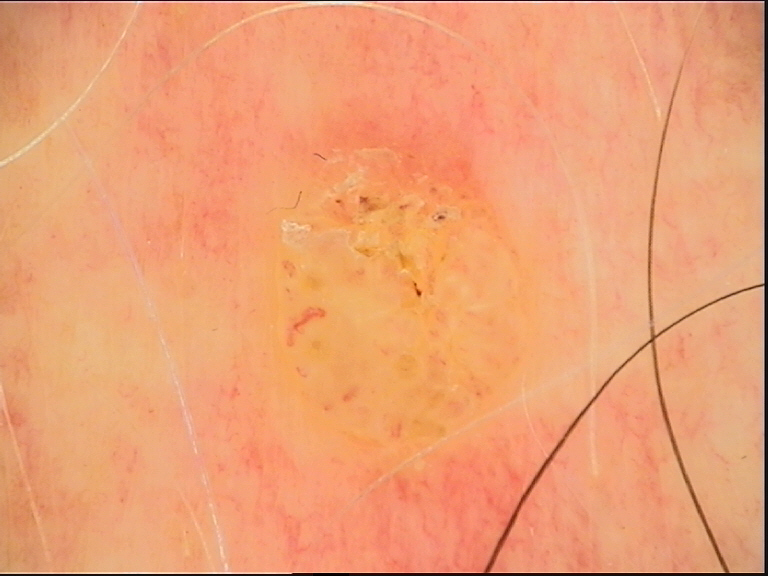Summary:
A dermoscopic close-up of a skin lesion.
Conclusion:
The diagnostic label was a seborrheic keratosis.